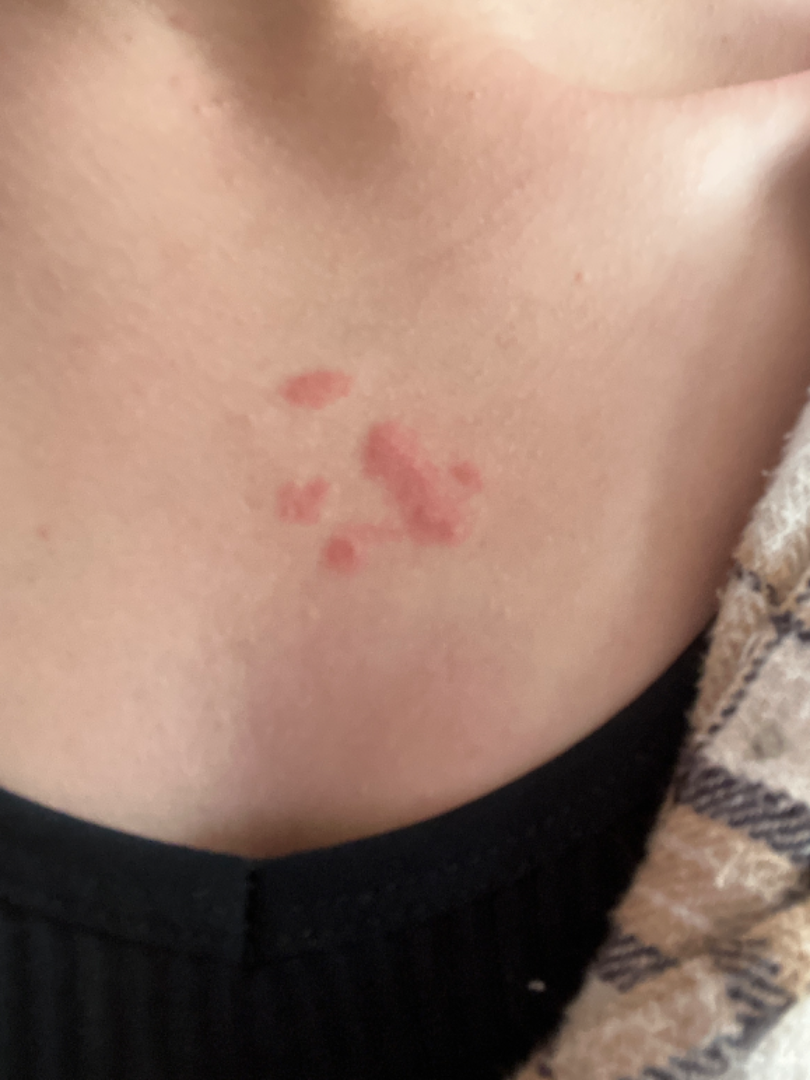Impression:
No differential diagnosis could be assigned on photographic review.
History:
Close-up view.